Close-up view · male subject, age 18–29 · the affected area is the back of the hand.
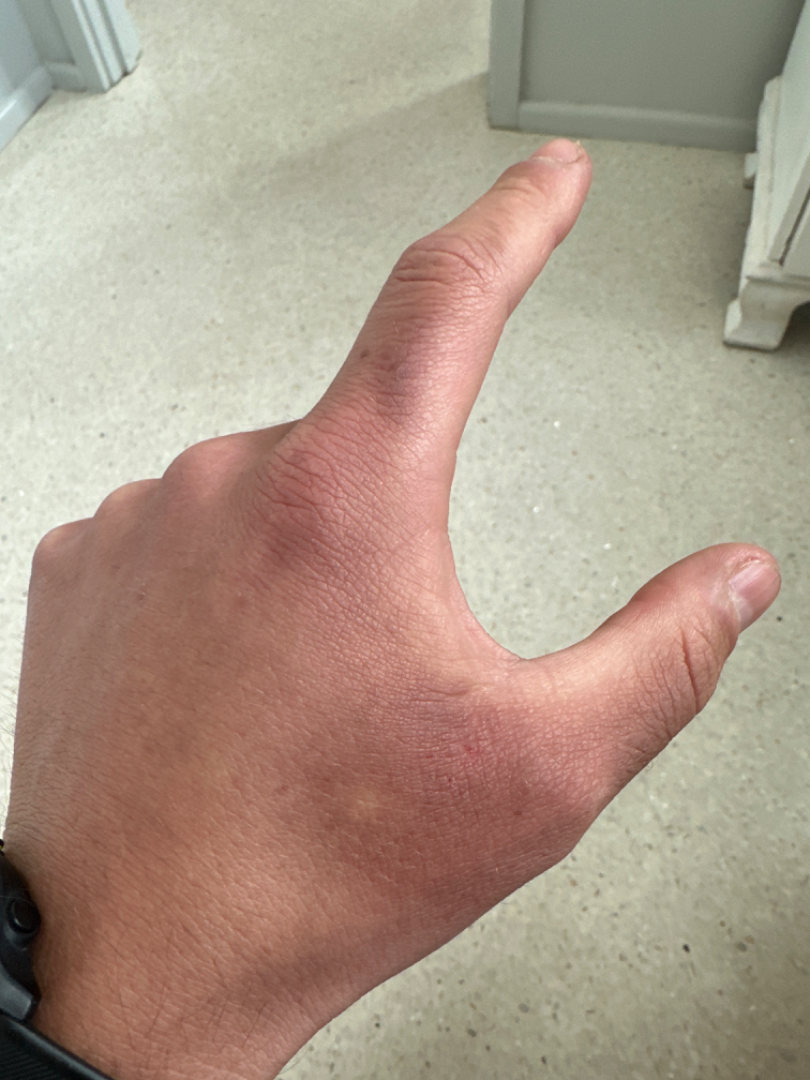Findings:
The reviewer was unable to grade this case for skin condition.